Symptoms reported: pain, darkening, enlargement and itching. Associated systemic symptoms include joint pain and shortness of breath. The patient is 60–69, female. The leg is involved. Close-up view: 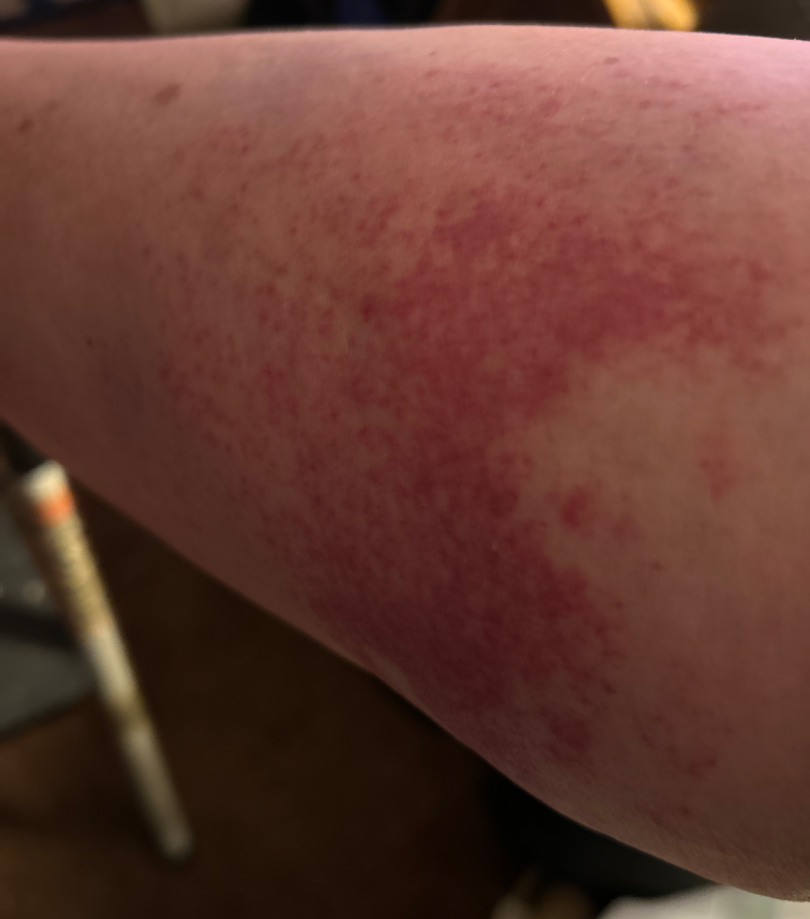On remote review of the image, in keeping with Leukocytoclastic Vasculitis.